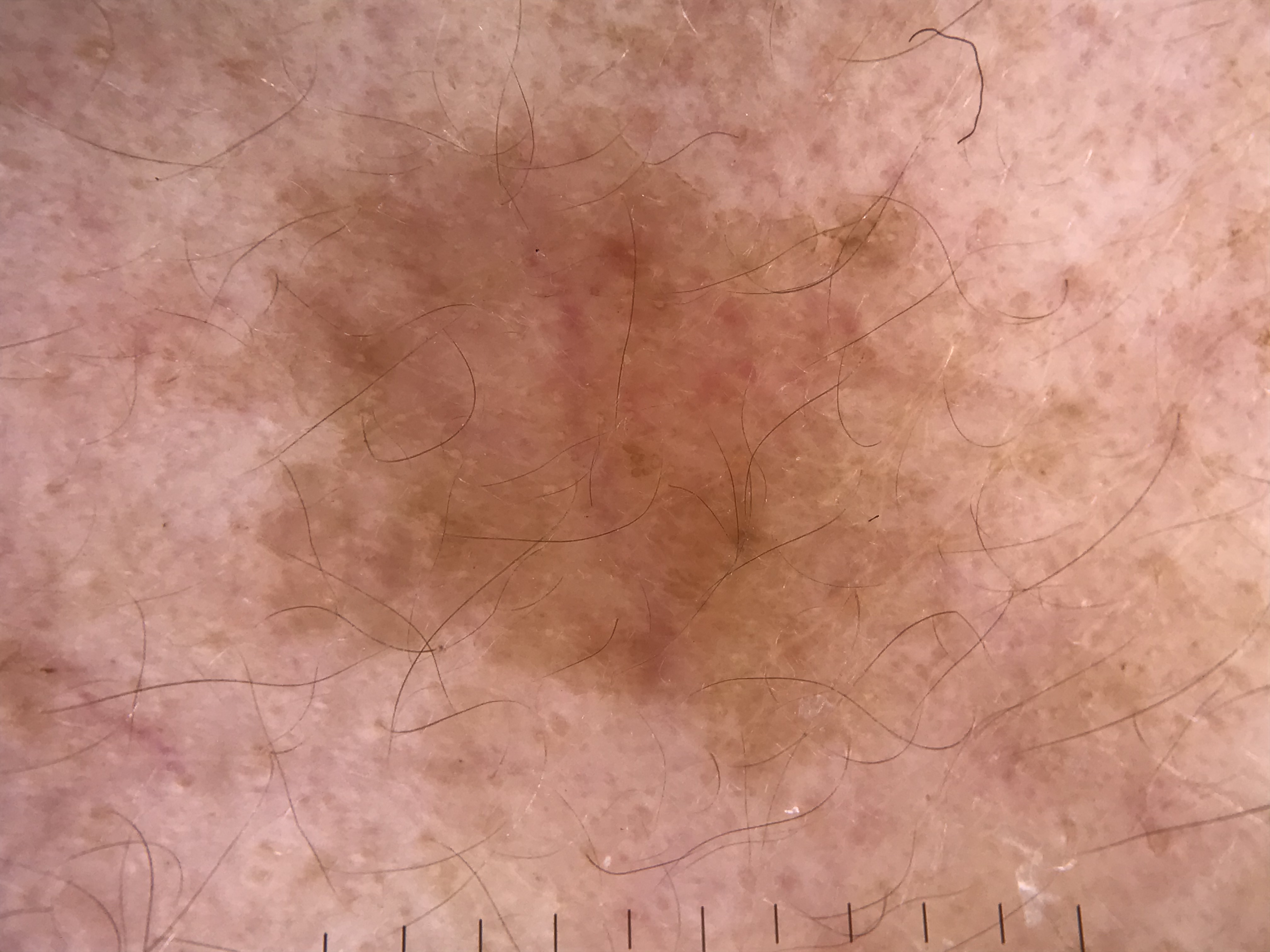Findings: A dermoscopy image of a single skin lesion. The morphology is that of a keratinocytic lesion. Conclusion: The diagnosis was a benign lesion — a seborrheic keratosis.